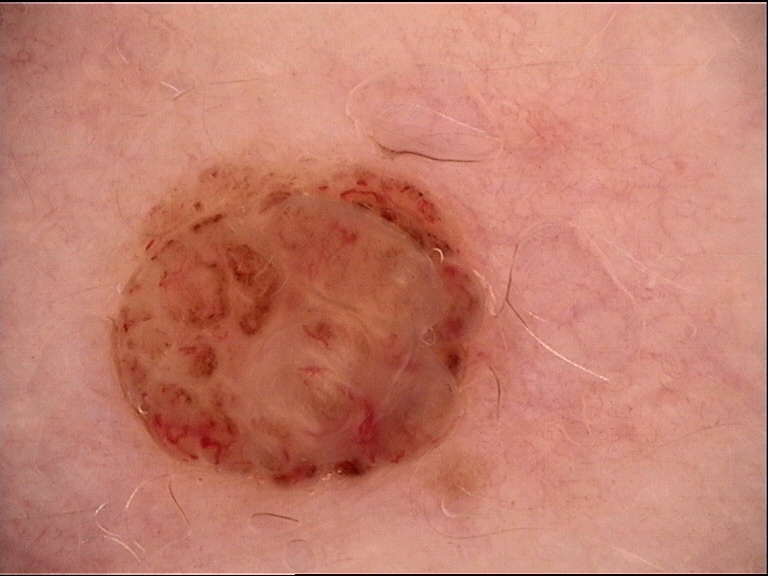<lesion>
  <diagnosis>
    <name>dermal nevus</name>
    <code>db</code>
    <malignancy>benign</malignancy>
    <super_class>melanocytic</super_class>
    <confirmation>expert consensus</confirmation>
  </diagnosis>
</lesion>